A close-up photograph. Located on the arm and leg: 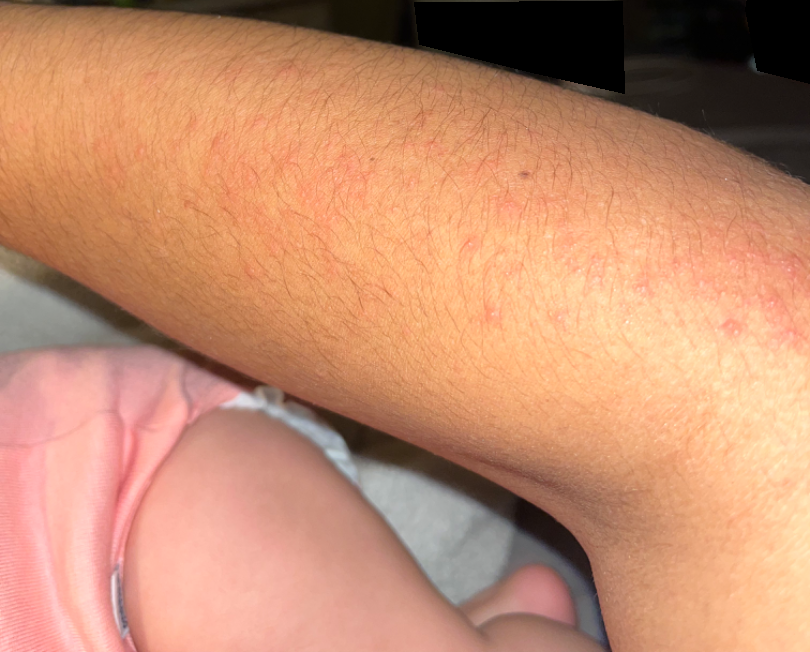| feature | finding |
|---|---|
| assessment | ungradable on photographic review |